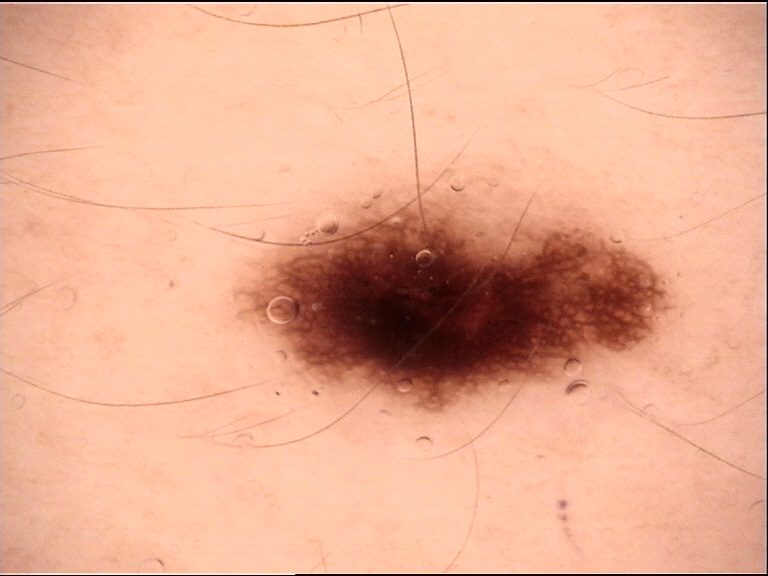Consistent with a junctional nevus.